The lesion is described as raised or bumpy · the patient also reports joint pain · present for one to four weeks · Fitzpatrick skin type II; non-clinician graders estimated Monk Skin Tone 2 or 4 (two reviewer pools disagreed) · located on the leg · reported lesion symptoms include enlargement and bothersome appearance · female subject, age 40–49 · the photograph was taken at a distance.
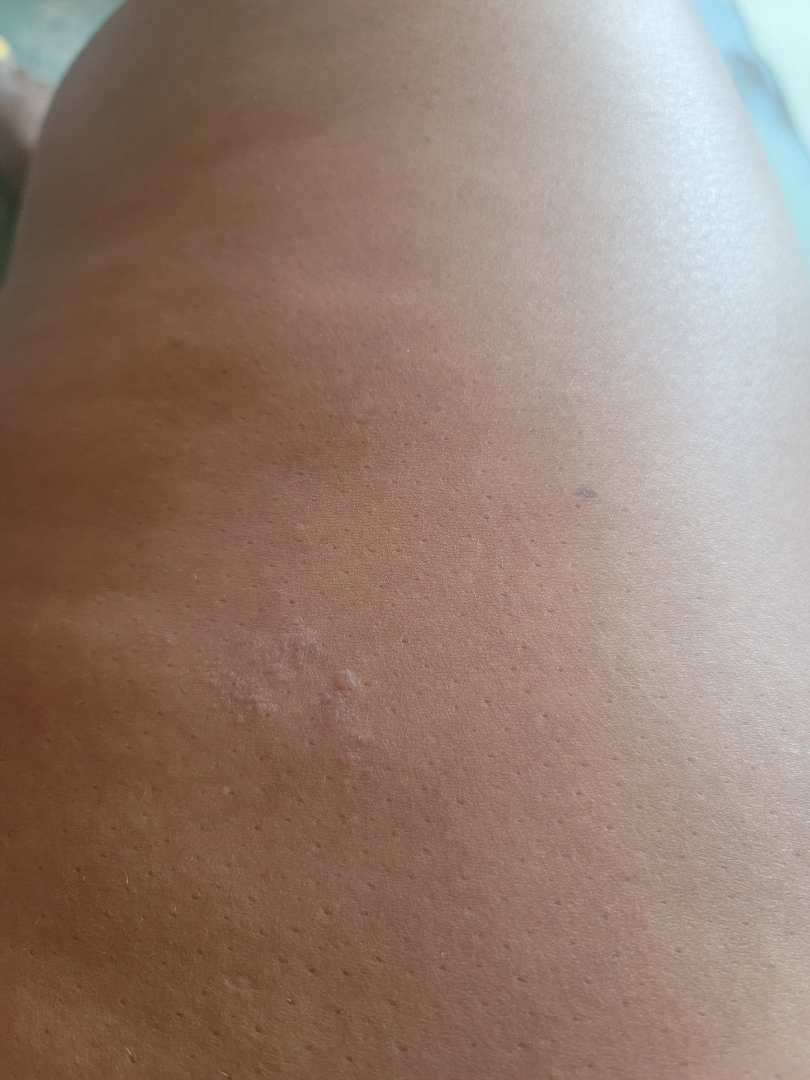Findings: On photographic review, Eczema (most likely); Verruca vulgaris (considered); Epidermal nevus (considered); SK/ISK (considered).